This image was taken at an angle. Located on the top or side of the foot — 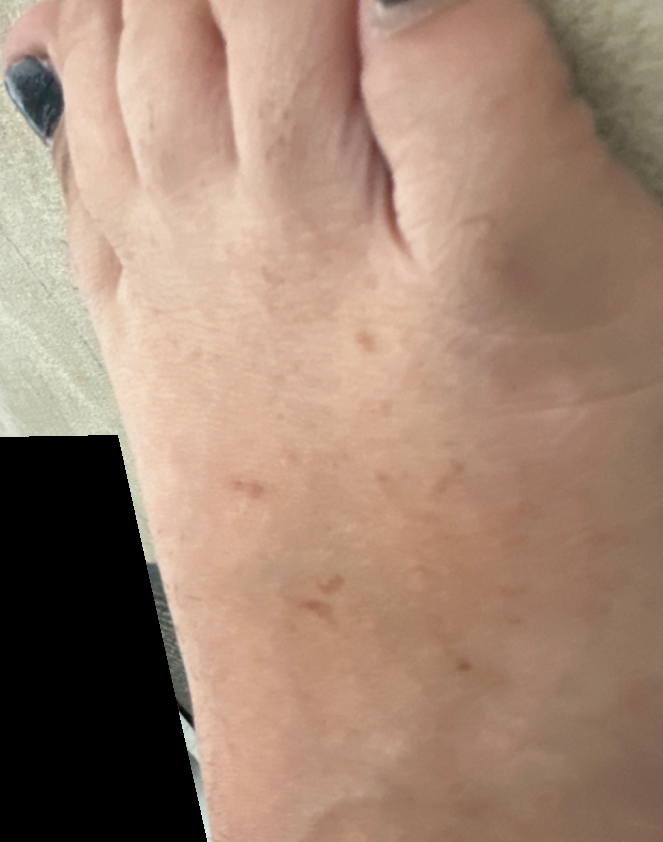| key | value |
|---|---|
| assessment | could not be assessed |